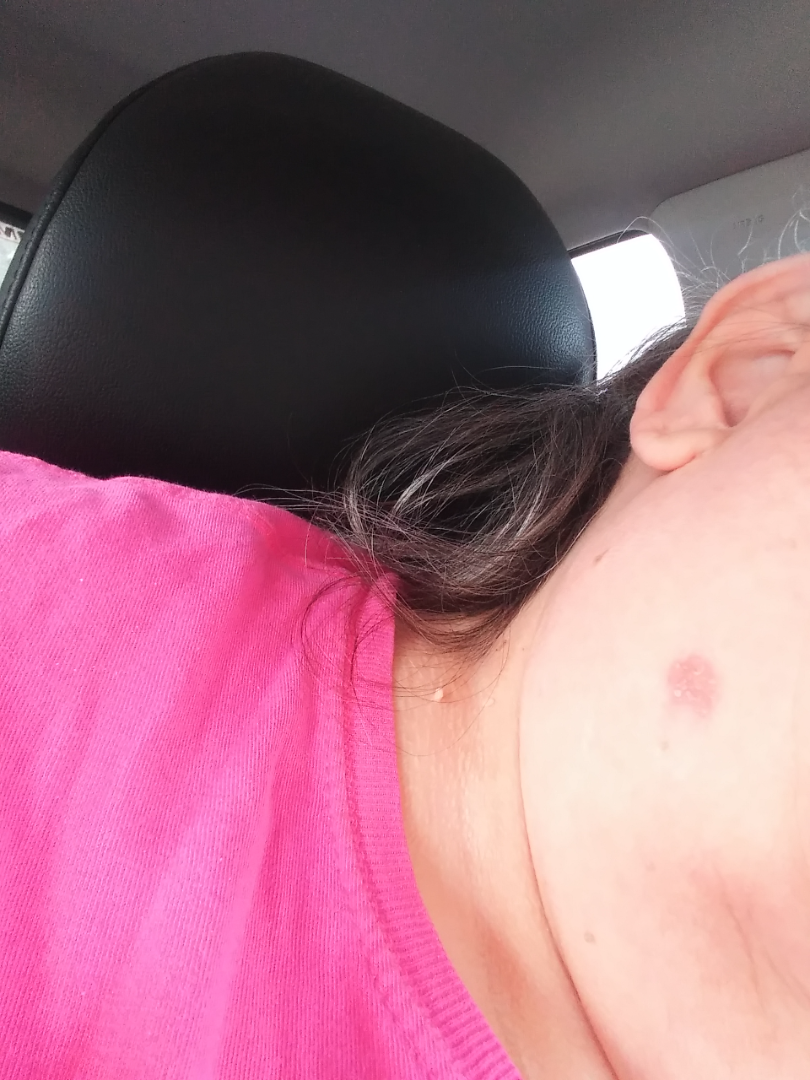assessment: indeterminate